The arm is involved. This image was taken at an angle. The patient is a female aged 40–49 — 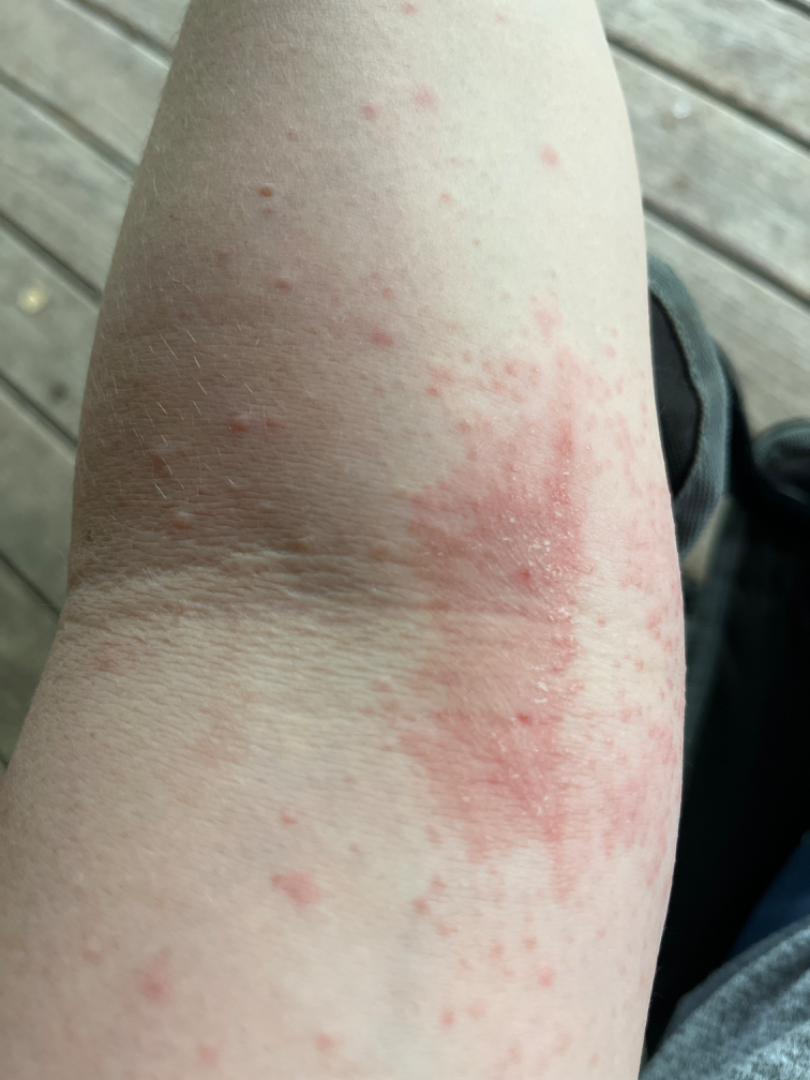{"differential": "Eczema"}